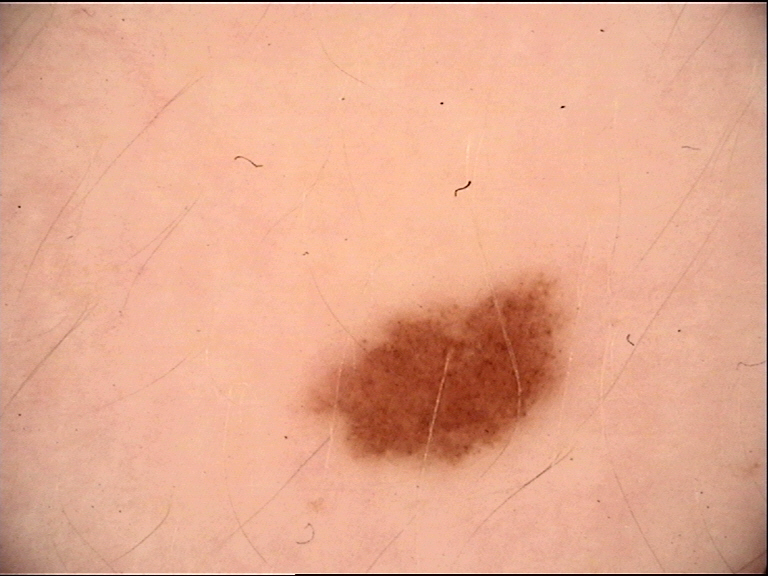A dermoscopic photograph of a skin lesion. The diagnostic label was a benign lesion — a dysplastic junctional nevus.